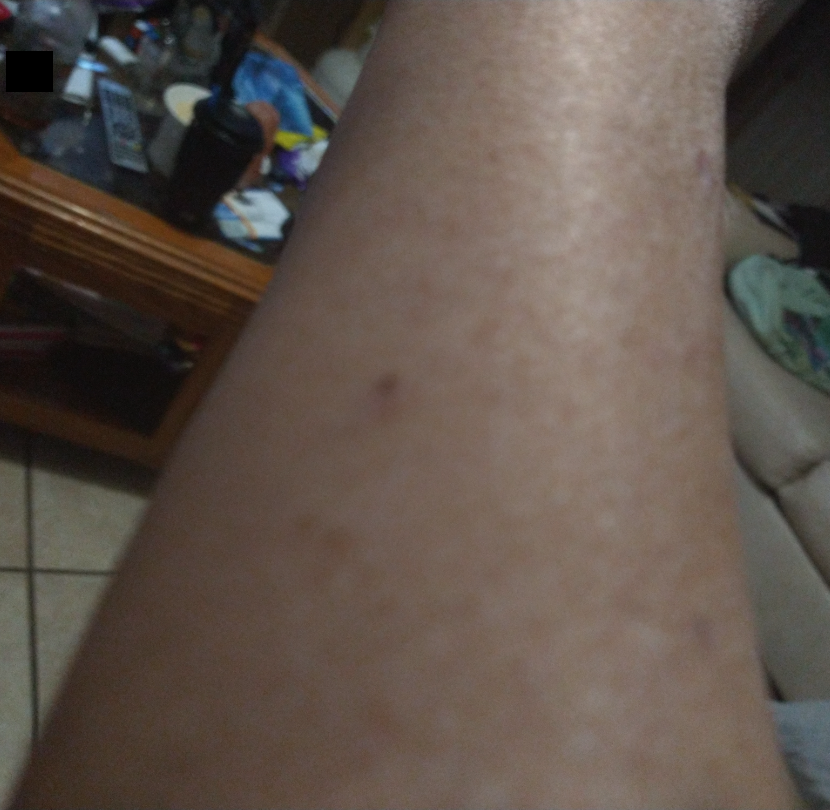<report>
  <assessment>could not be assessed</assessment>
  <symptoms>pain, burning, itching</symptoms>
  <shot_type>at an angle</shot_type>
  <body_site>sole of the foot, arm, head or neck</body_site>
  <duration>one to four weeks</duration>
  <texture>raised or bumpy, rough or flaky</texture>
  <patient_category>a rash</patient_category>
</report>